A dermoscopic close-up of a skin lesion:
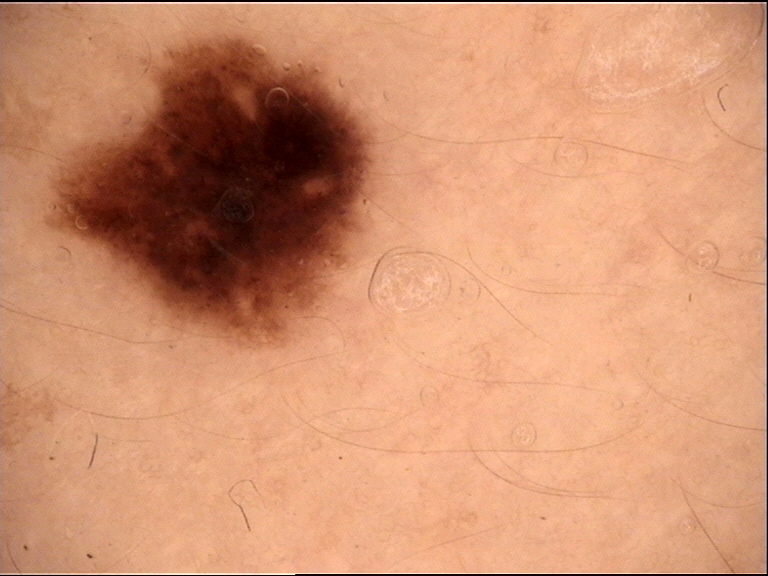<lesion>
<diagnosis>
<name>dysplastic junctional nevus</name>
<code>jd</code>
<malignancy>benign</malignancy>
<super_class>melanocytic</super_class>
<confirmation>expert consensus</confirmation>
</diagnosis>
</lesion>